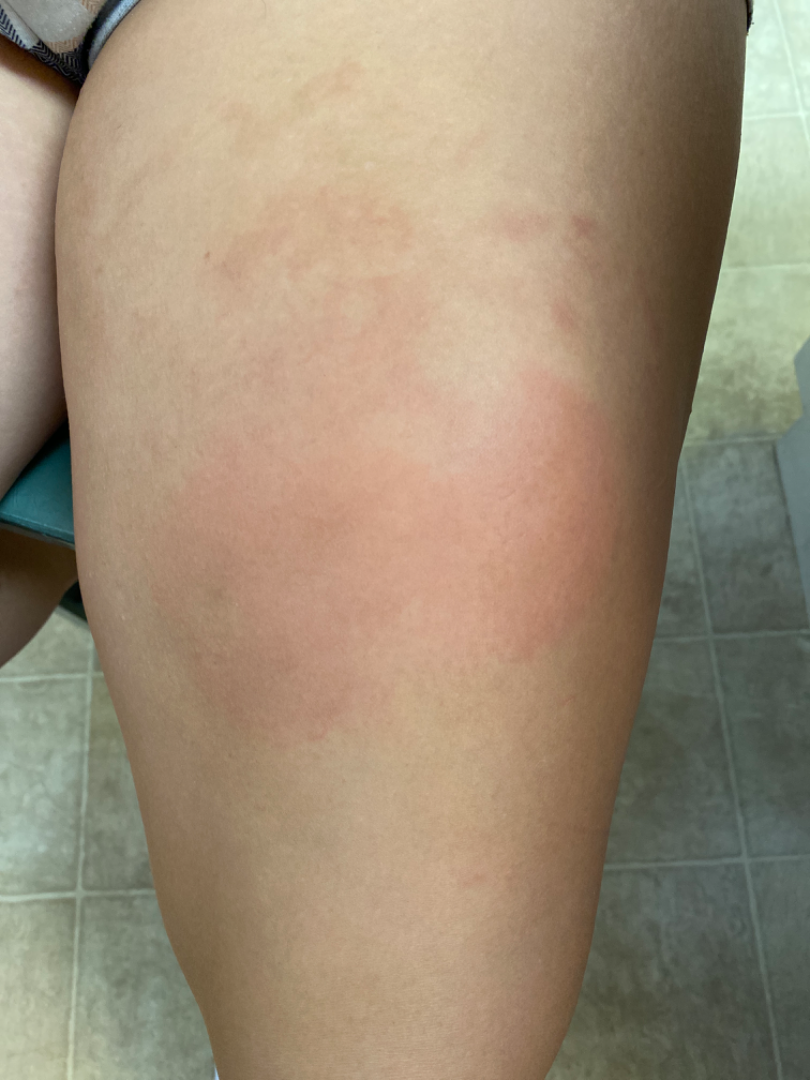Q: What is the dermatologist's impression?
A: reviewed remotely by one dermatologist: favoring Hypersensitivity; with consideration of Urticaria